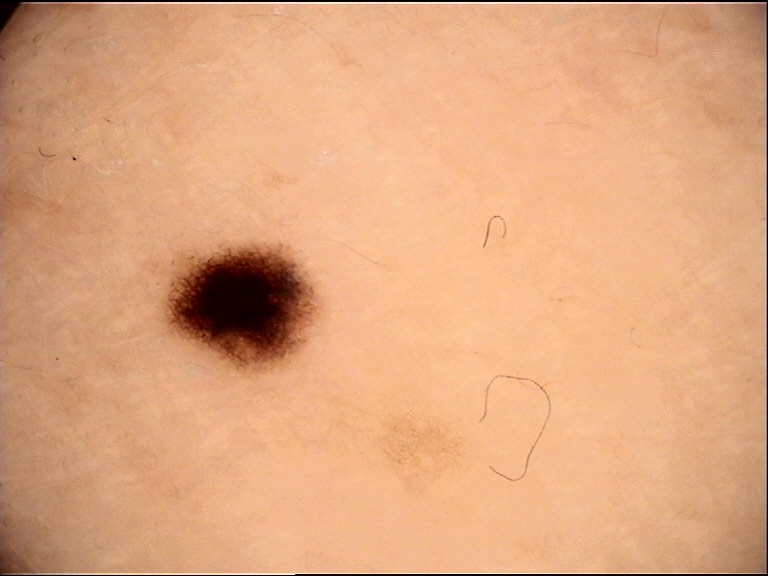Consistent with a banal lesion — a junctional nevus.